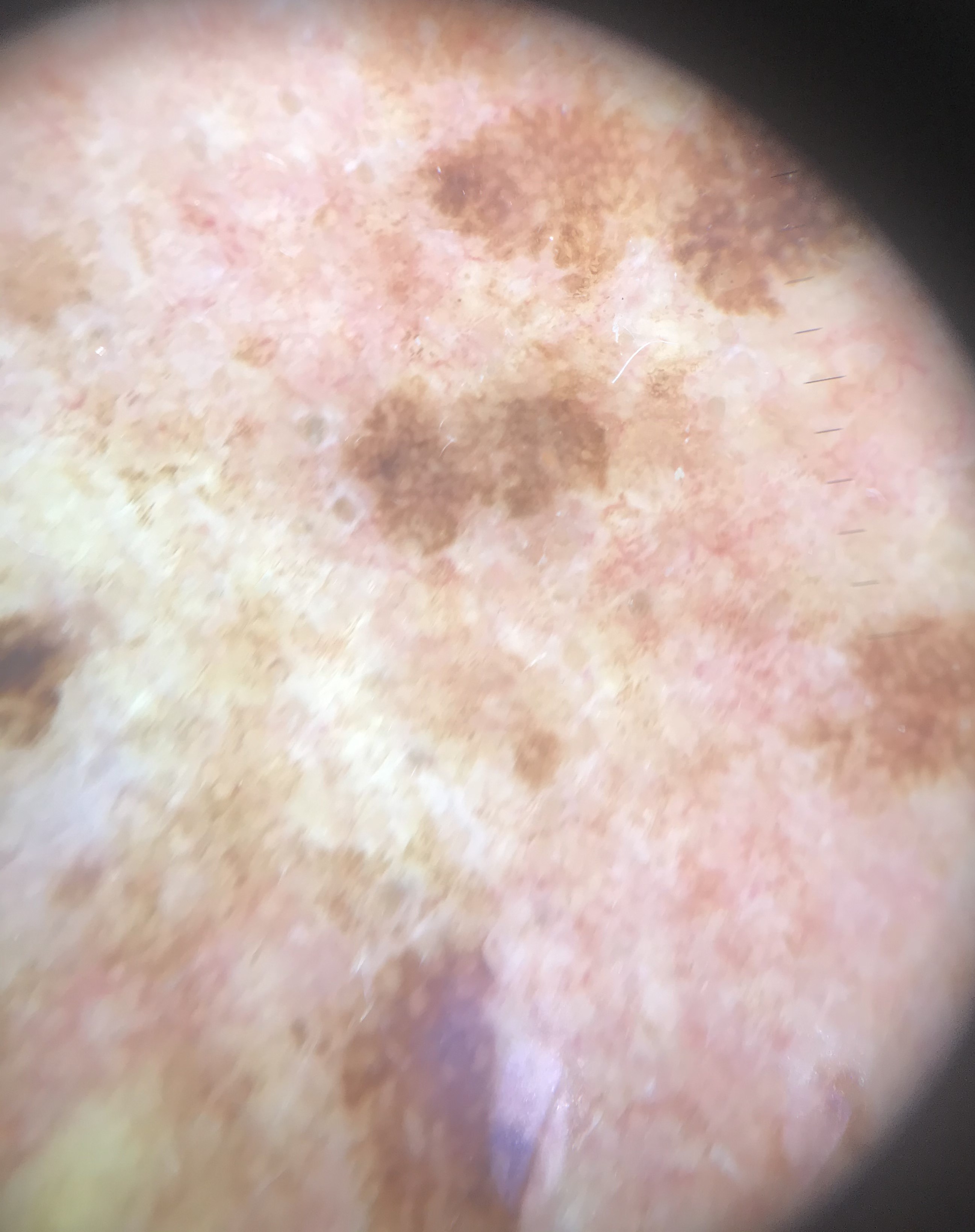Diagnosed as a seborrheic keratosis.